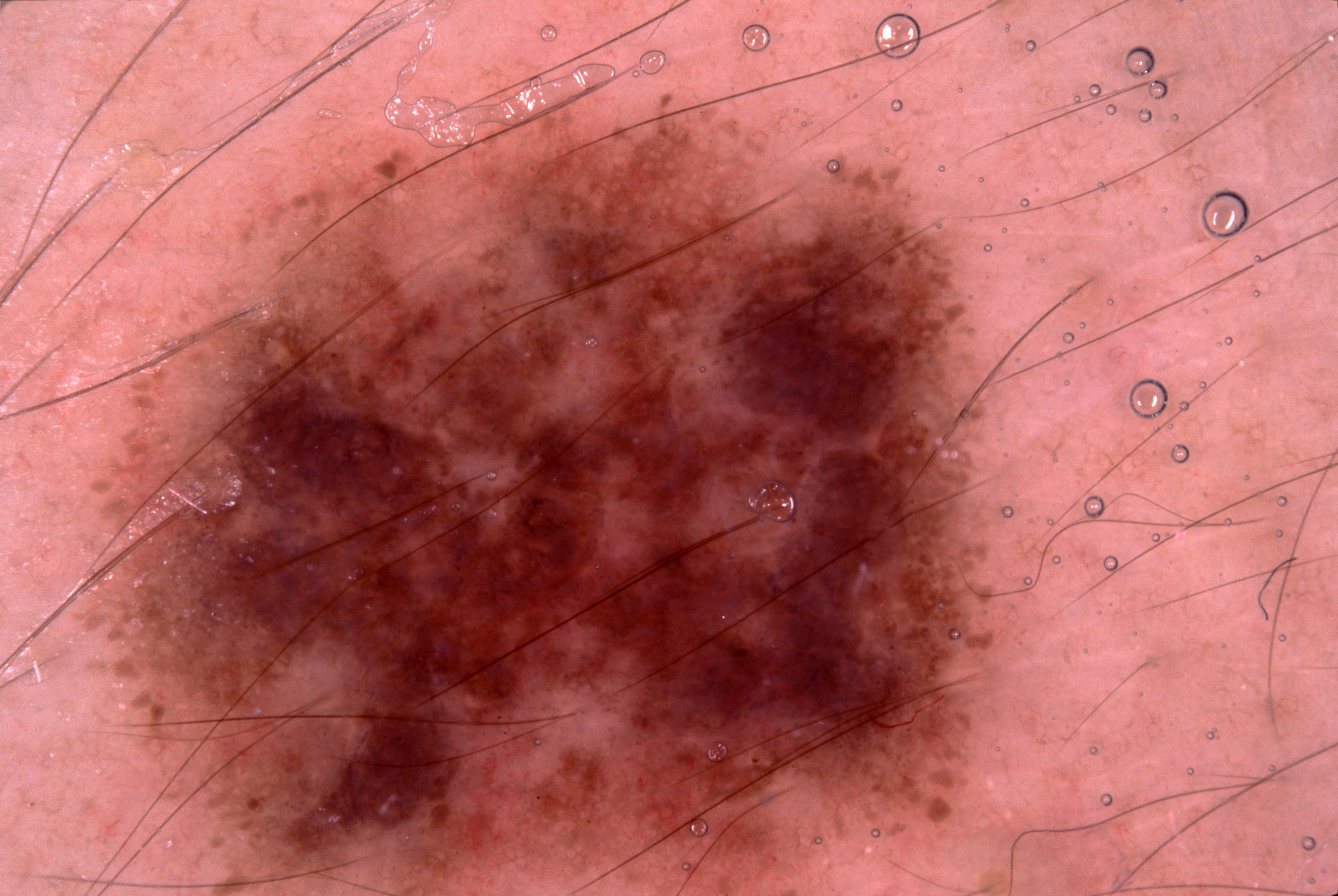Notes:
• image · dermoscopy
• subject · male, about 25 years old
• lesion extent · ~57% of the field
• dermoscopic findings · pigment network; absent: streaks, milia-like cysts, and negative network
• location · bbox=[68, 65, 1055, 895]
• assessment · a melanocytic nevus